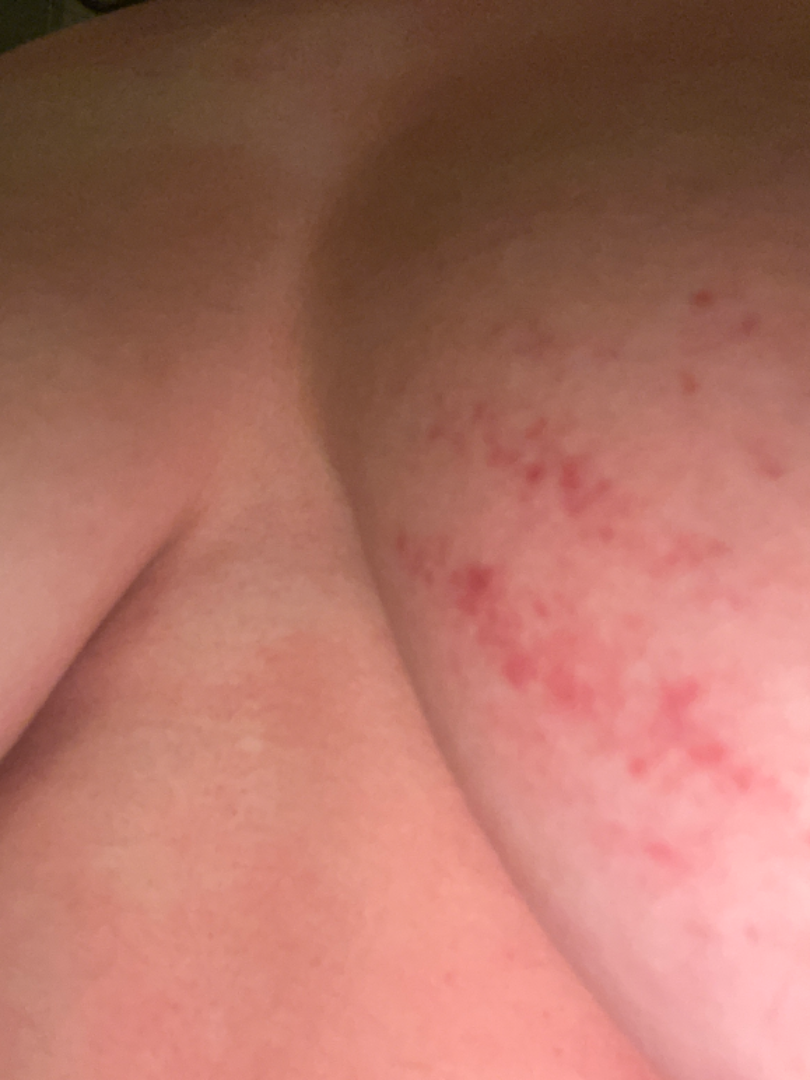photo taken: close-up
contributor: female, age 18–29
assessment: ecchymoses (most likely); Eczema (considered)